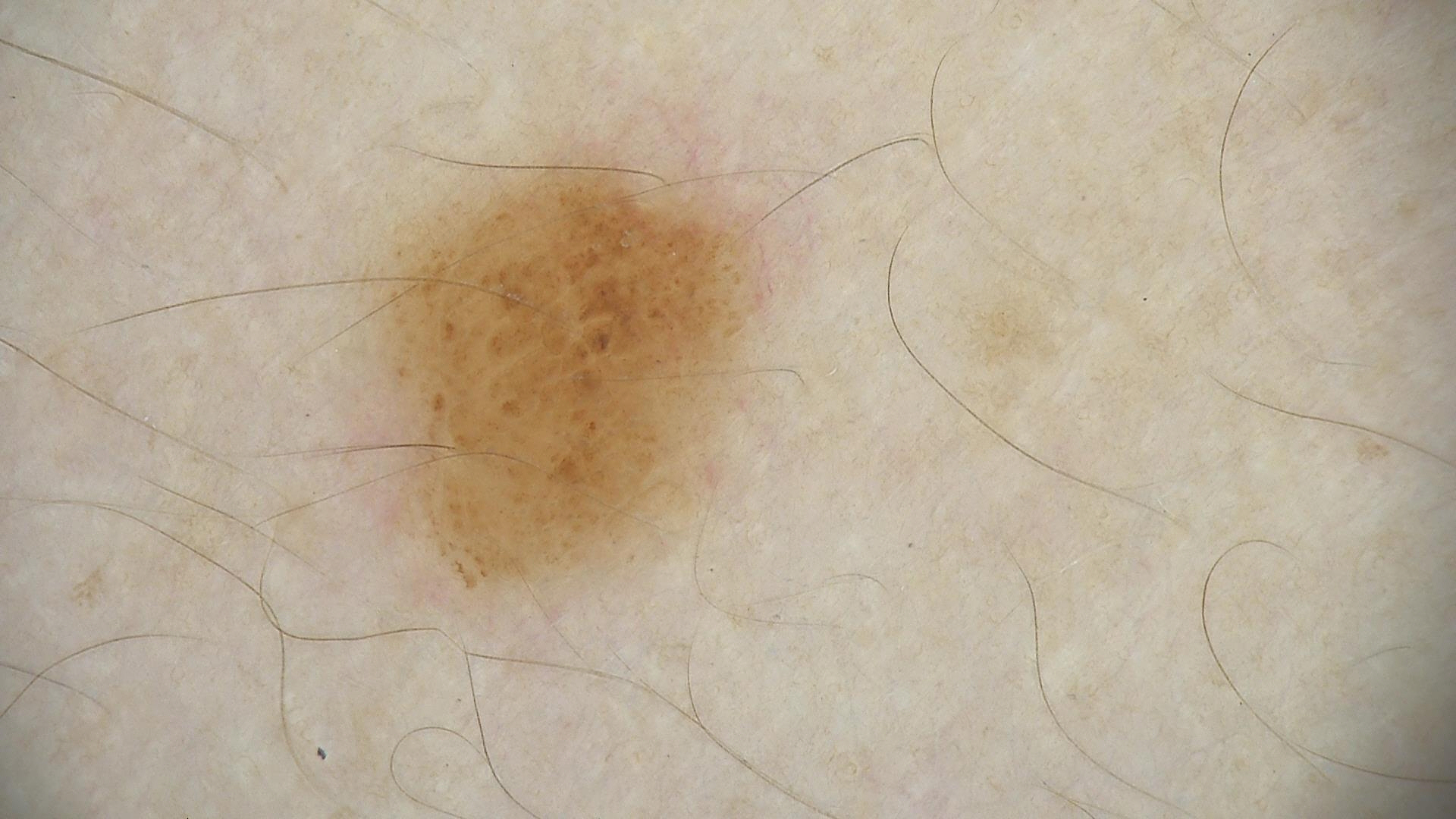Q: What is the diagnosis?
A: dysplastic junctional nevus (expert consensus)